An image taken at an angle.
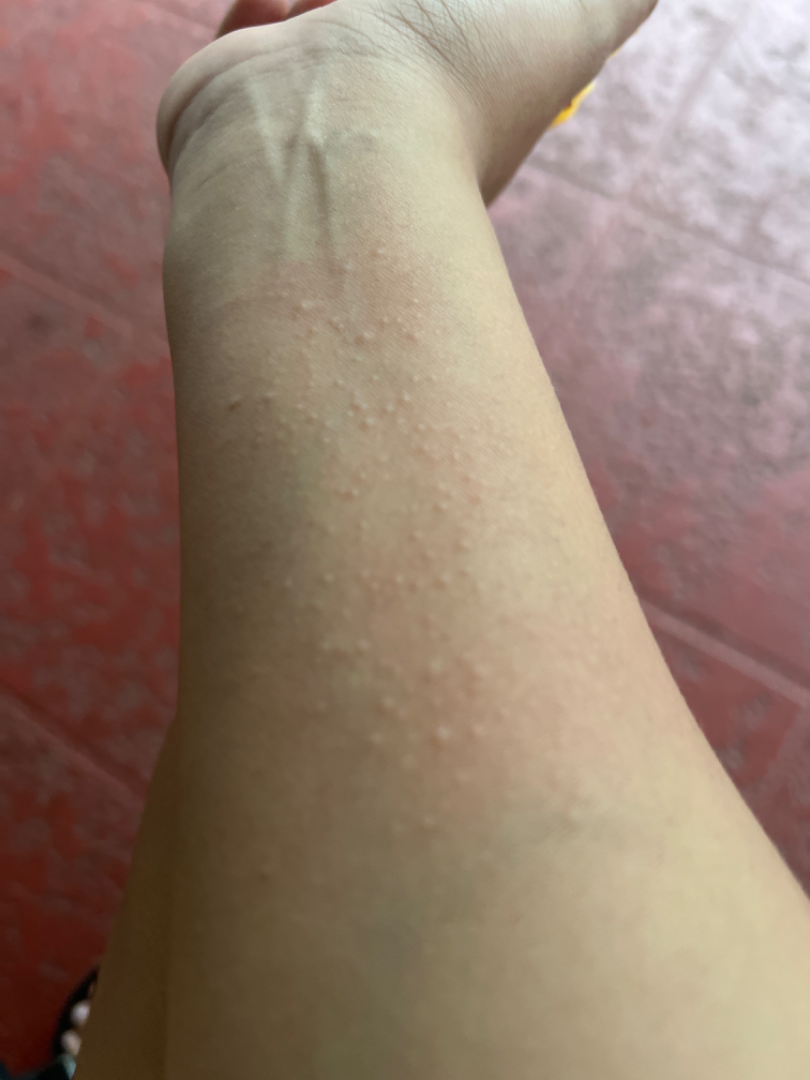{"differential": {"leading": ["Lichen nitidus"], "considered": ["Miliaria", "Allergic Contact Dermatitis"]}}